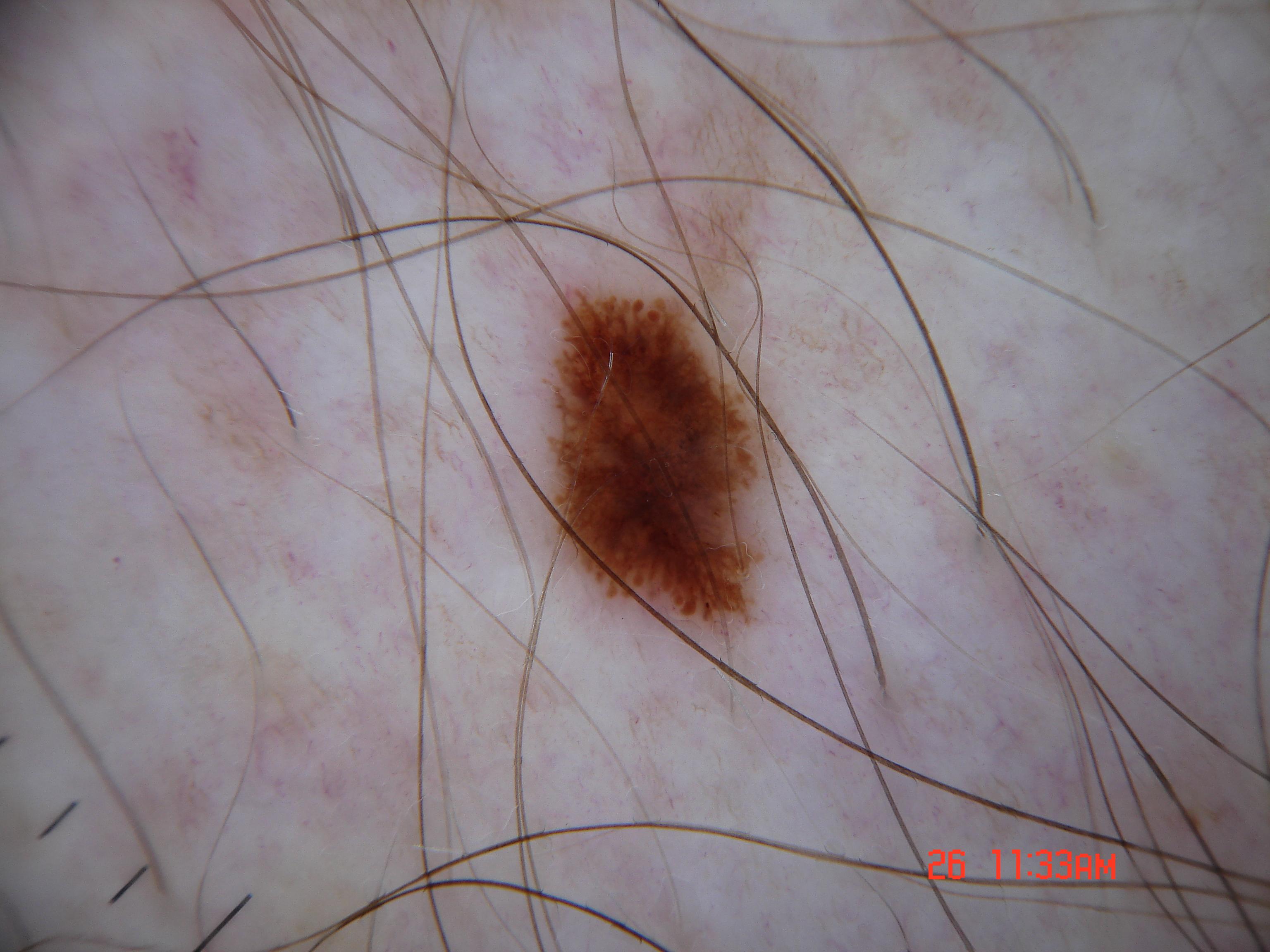Case summary:
• patient · male, aged around 55
• image · dermoscopic image
• lesion location · [536,277,777,631]
• dermoscopic pattern · streaks, globules, and pigment network; absent: negative network and milia-like cysts
• diagnosis · a melanoma